A dermoscopic close-up of a skin lesion.
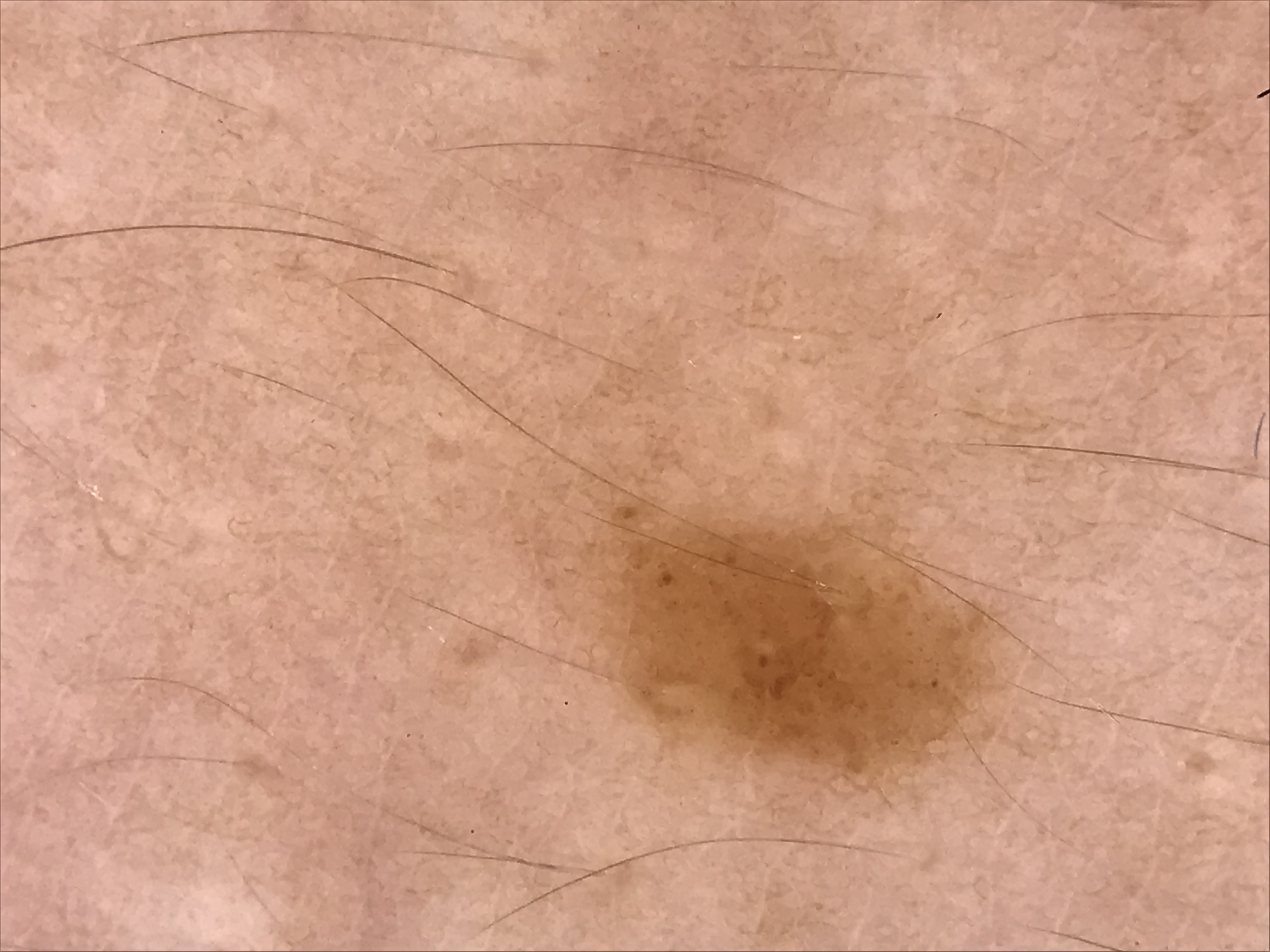Case:
This is a banal lesion.
Impression:
Labeled as a junctional nevus.